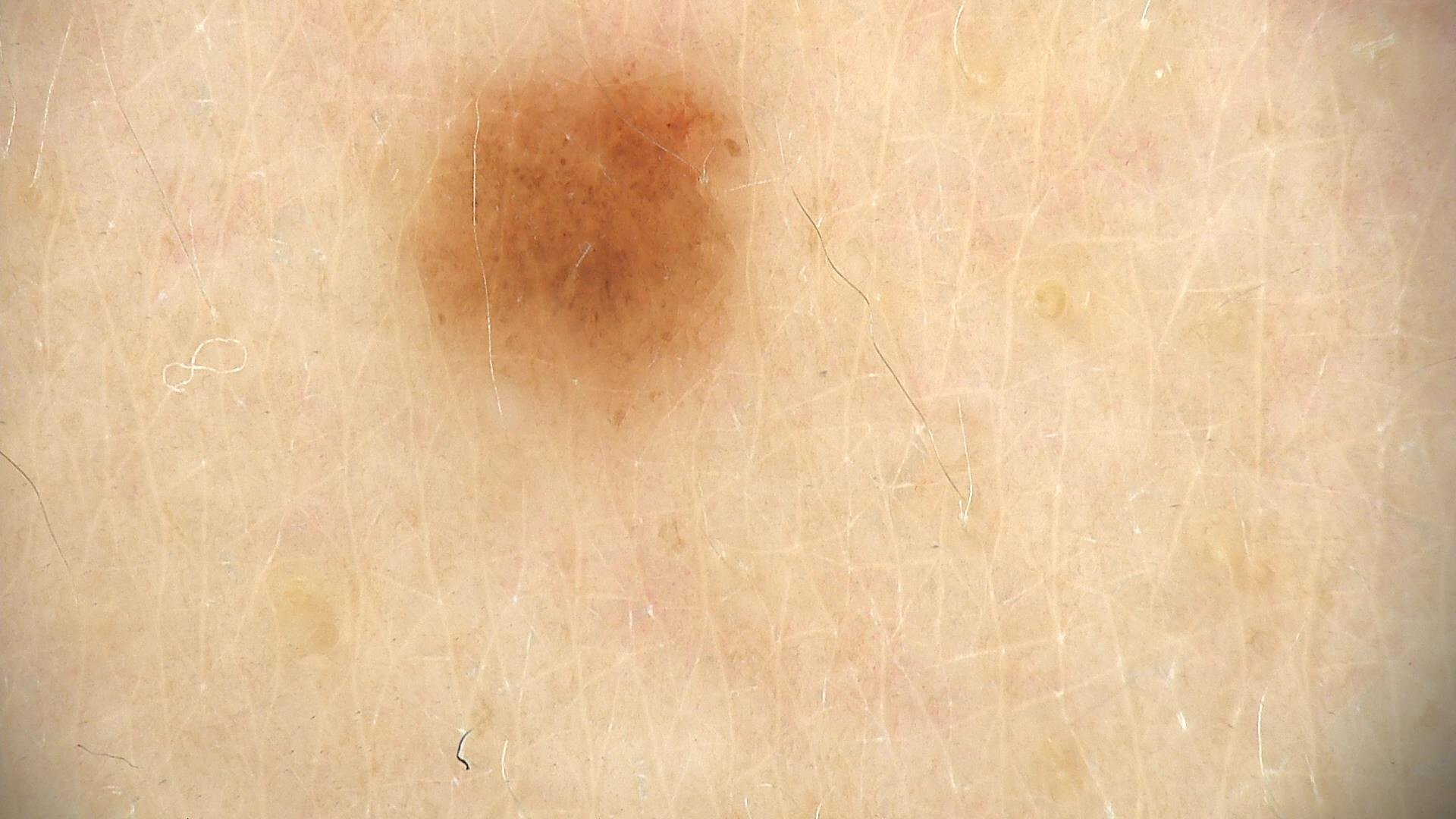modality — dermoscopy | class — dysplastic compound nevus (expert consensus).